Contact-polarized dermoscopy of a skin lesion. A female subject aged 63 to 67. Fitzpatrick skin type I. The chart notes a prior melanoma — 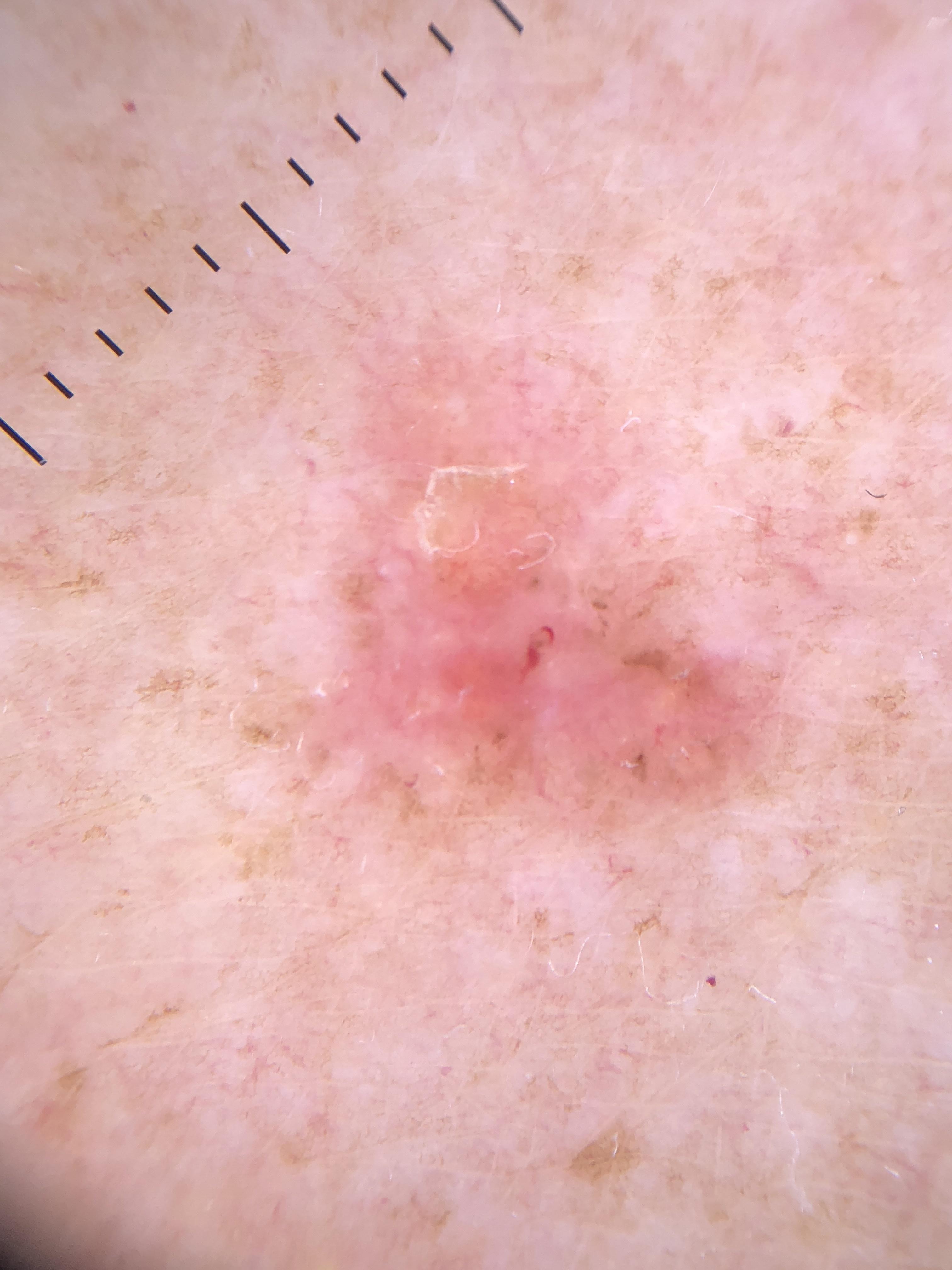The lesion is on the posterior trunk. Histopathological examination showed a tumor of follicular differentiation — a basal cell carcinoma.